The patient reported no systemic symptoms, this is a close-up image, the sole of the foot is involved, the subject is a female aged 18–29, the contributor notes the lesion is fluid-filled and flat, reported duration is less than one week: 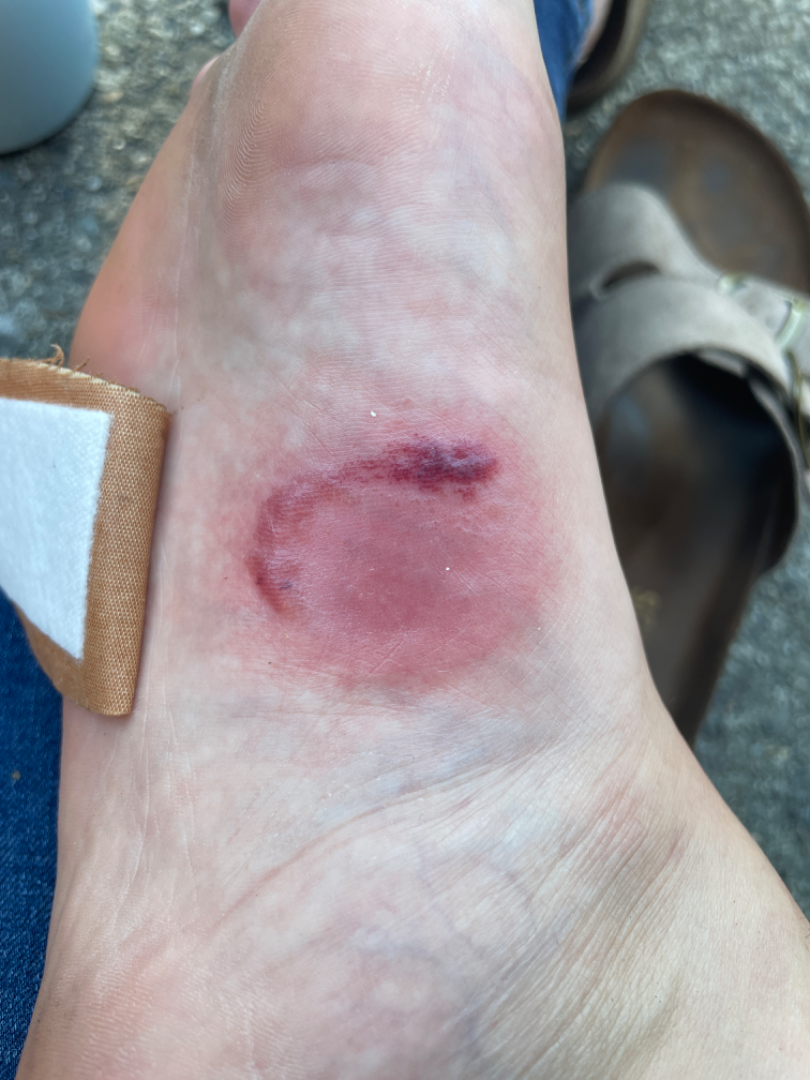The skin findings could not be characterized from the image.